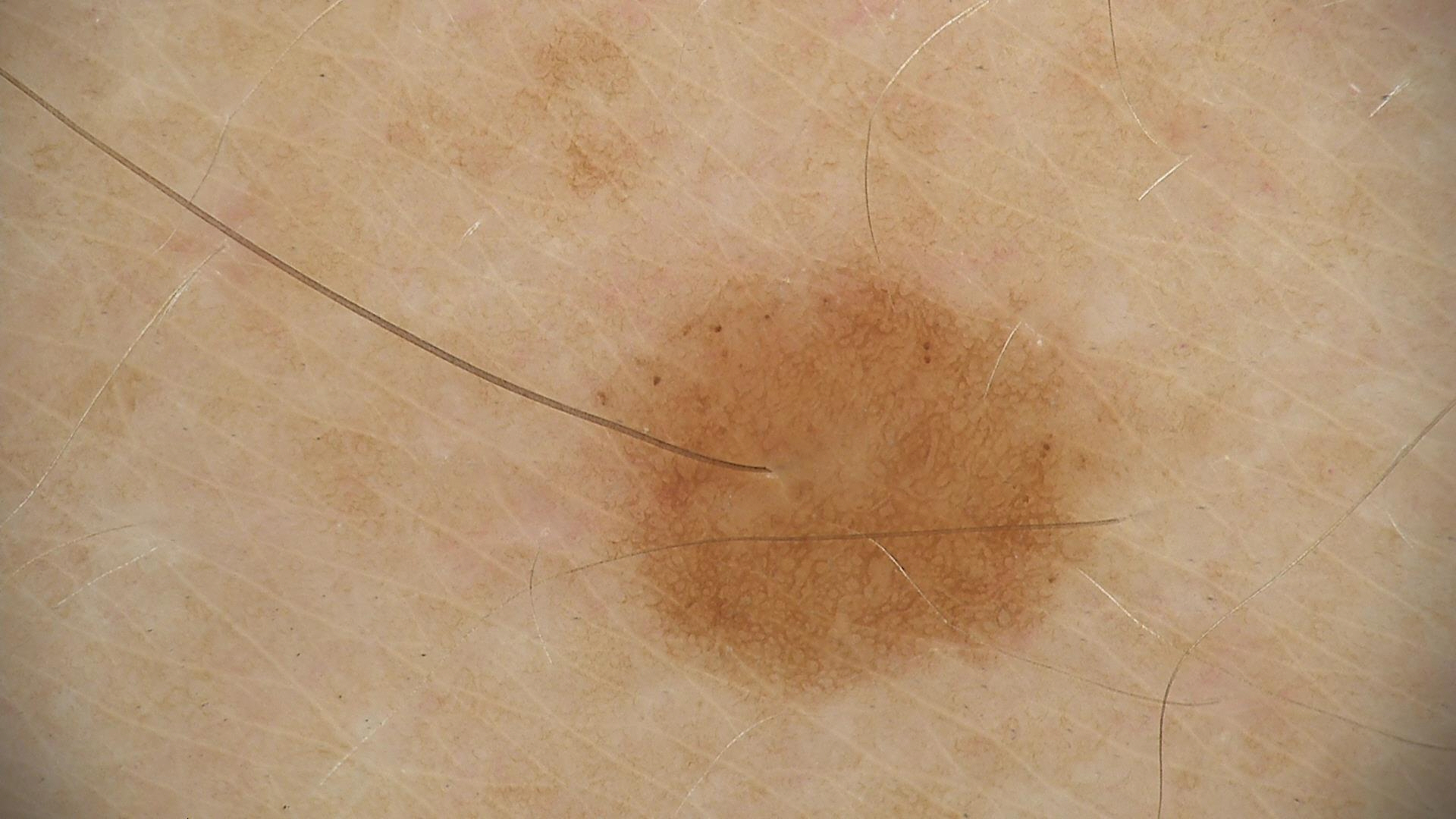Consistent with a benign lesion — a dysplastic junctional nevus.